Dermoscopy of a skin lesion: 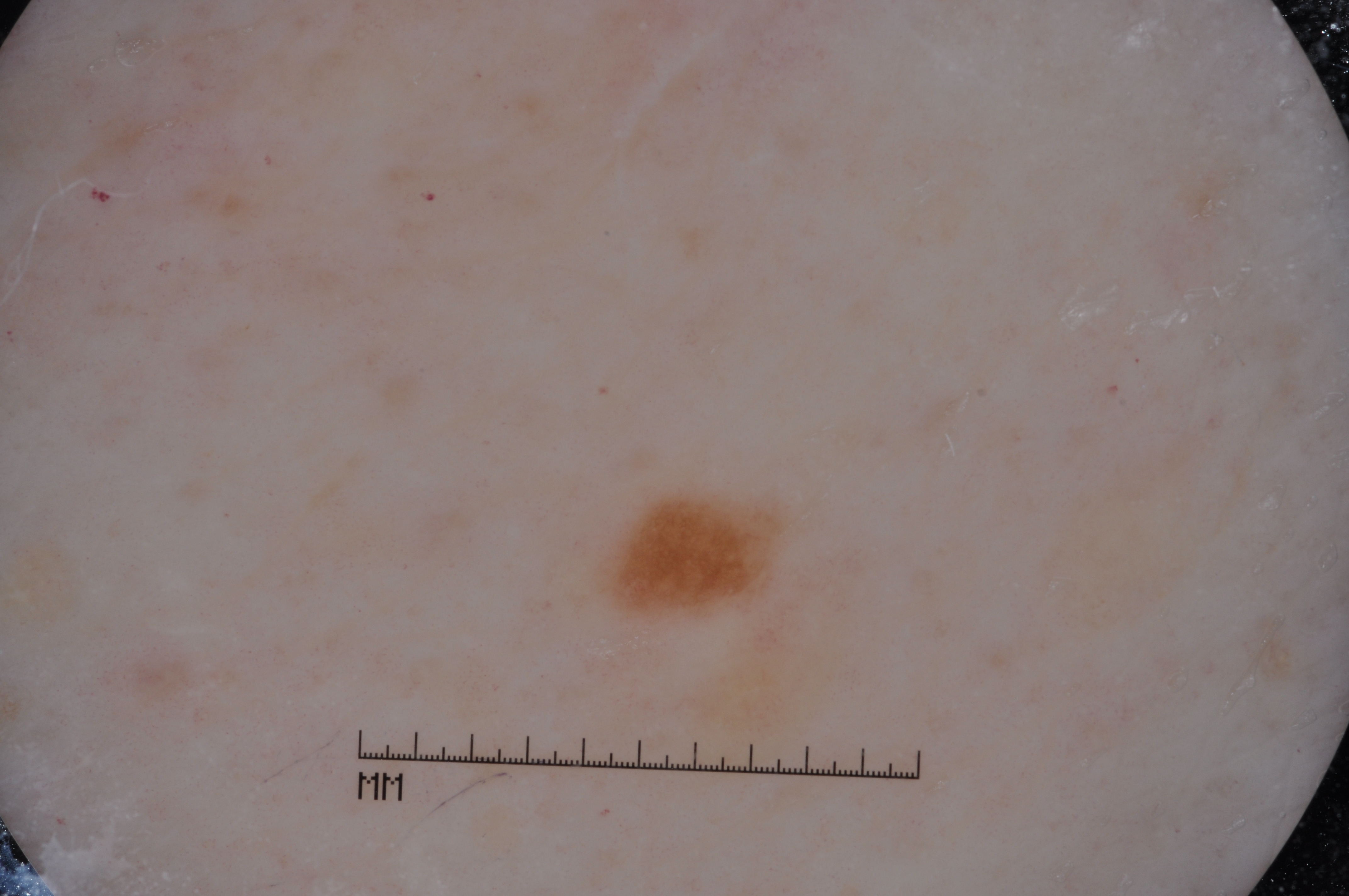Case summary: The dermoscopic pattern shows pigment network, with no negative network, streaks, or milia-like cysts. As (left, top, right, bottom), the lesion occupies the region [611,497,780,609]. Assessment: Clinically diagnosed as a melanocytic nevus.